A skin lesion imaged with a dermatoscope:
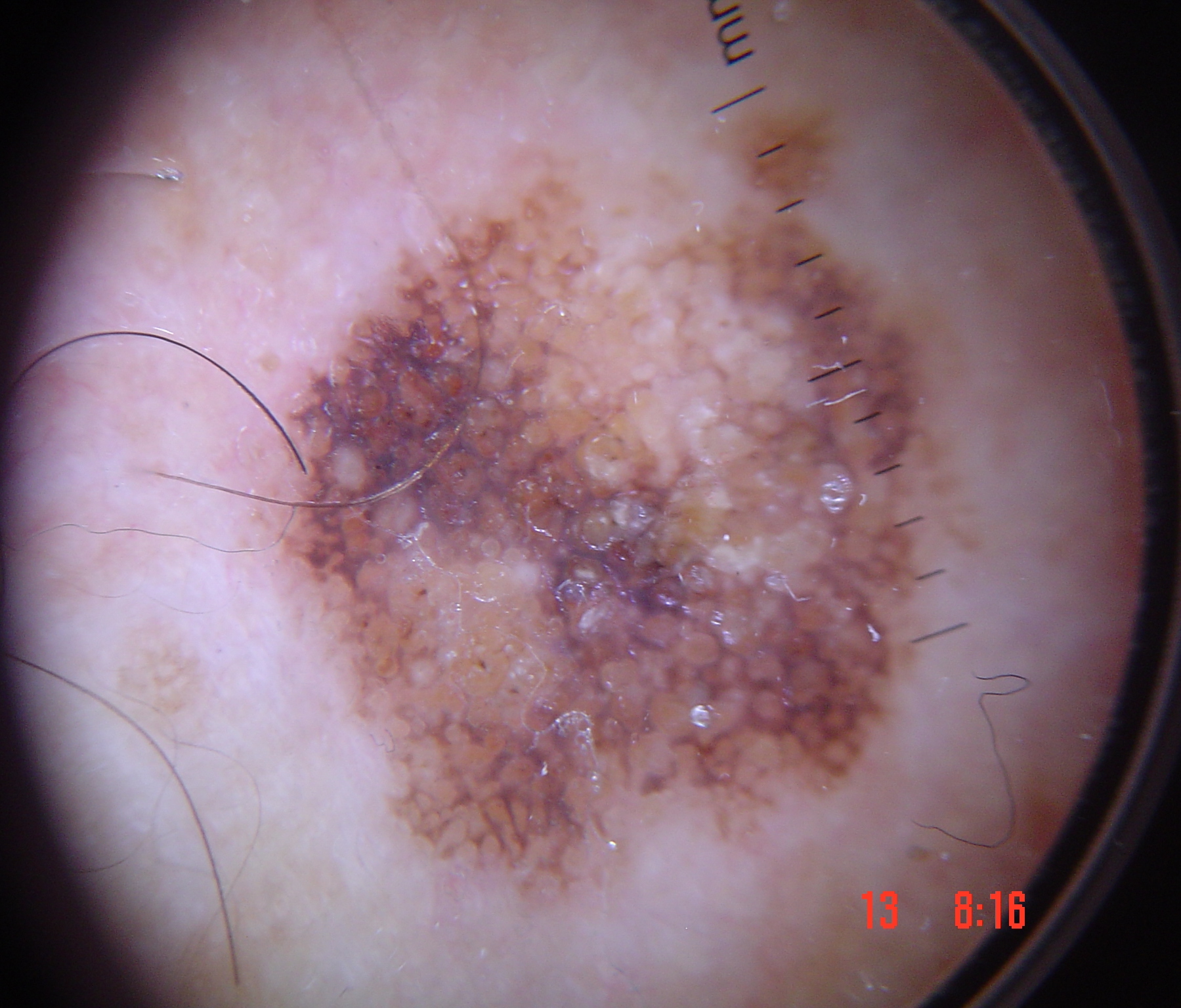Case: This is a keratinocytic lesion. Impression: Diagnosed as a seborrheic keratosis.